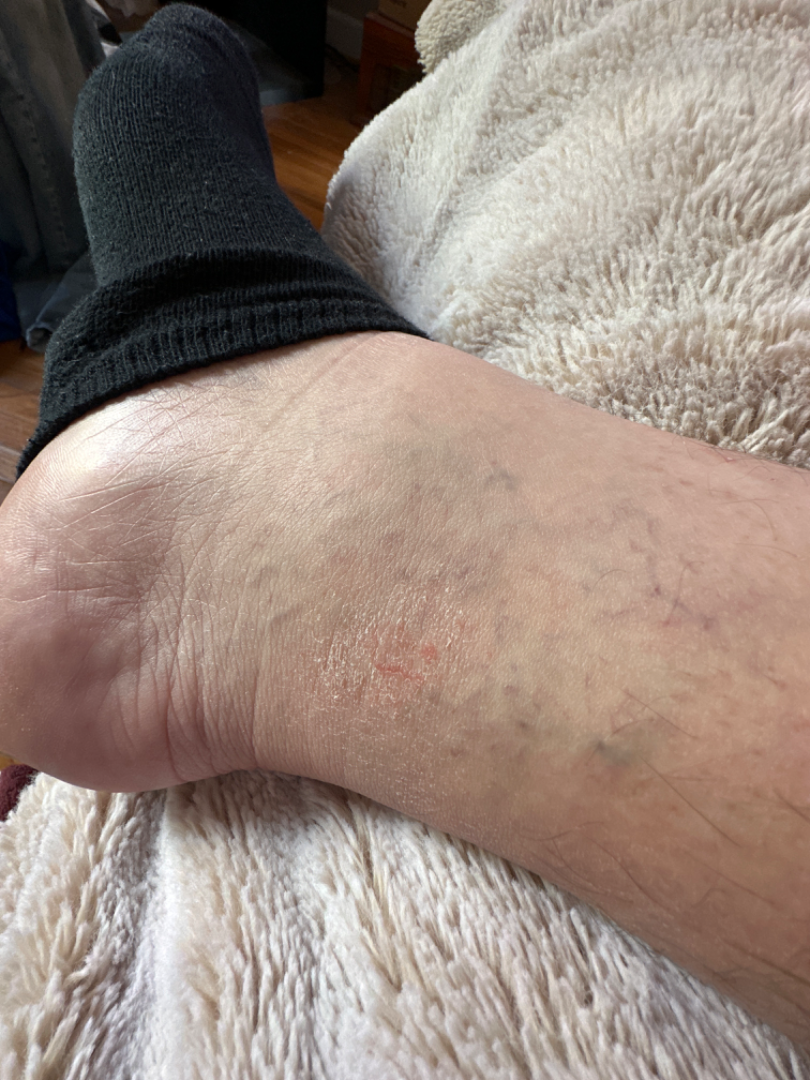Findings:
On dermatologist assessment of the image, Eczema (possible); Stasis Dermatitis (possible).